The lesion involves the arm; the lesion is associated with itching; skin tone: Fitzpatrick I; female subject, age 18–29; a close-up photograph; texture is reported as raised or bumpy and flat; present for about one day; self-categorized by the patient as a rash:
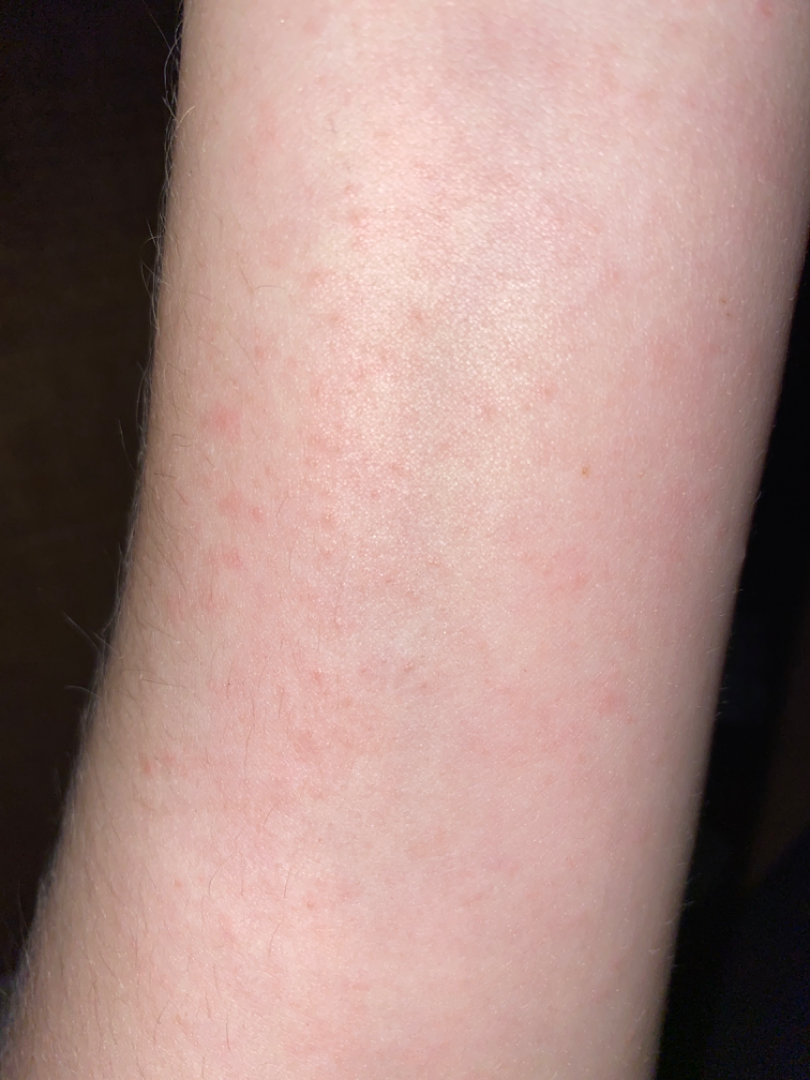The case was indeterminate on photographic review.